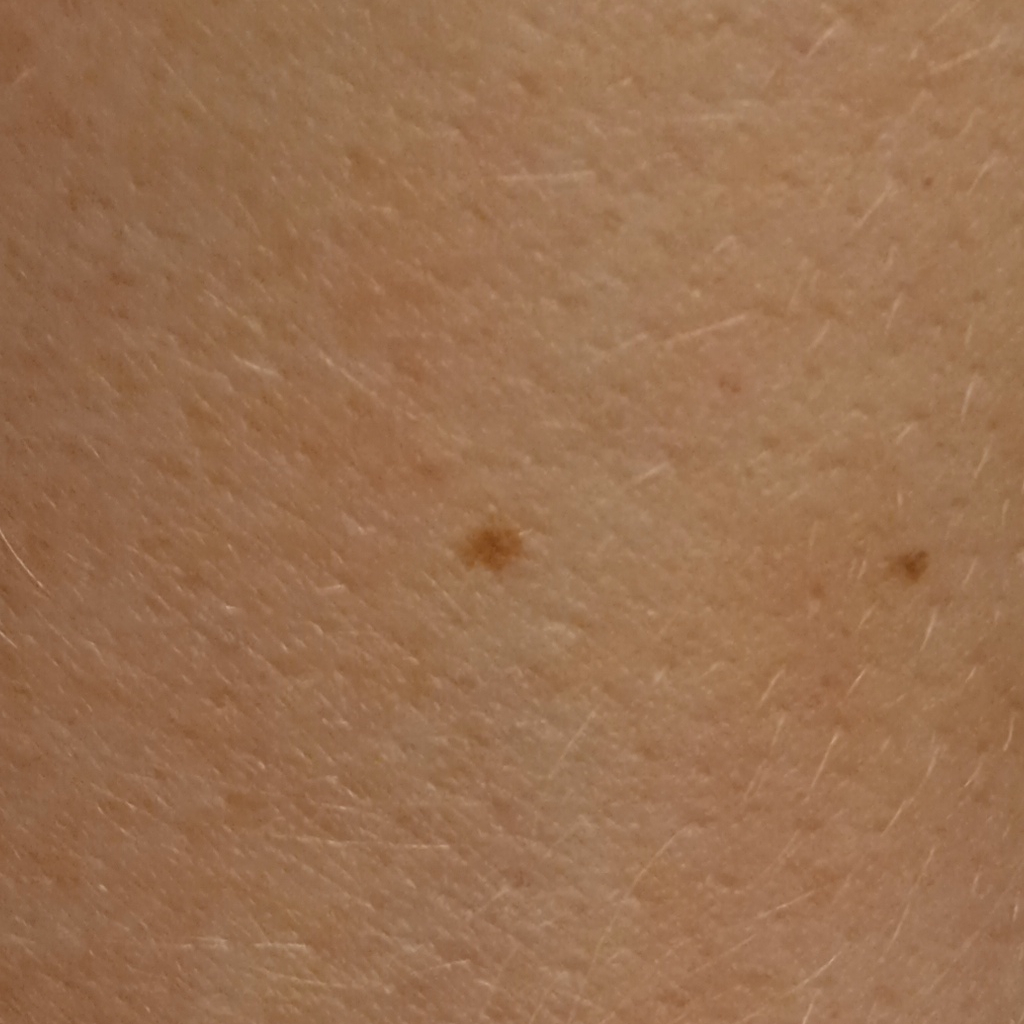The lesion was assessed as a melanocytic nevus.